Reported lesion symptoms include bothersome appearance and itching, the patient reports the lesion is raised or bumpy, the patient considered this a rash, present for about one day, the front of the torso is involved, the photograph was taken at an angle:
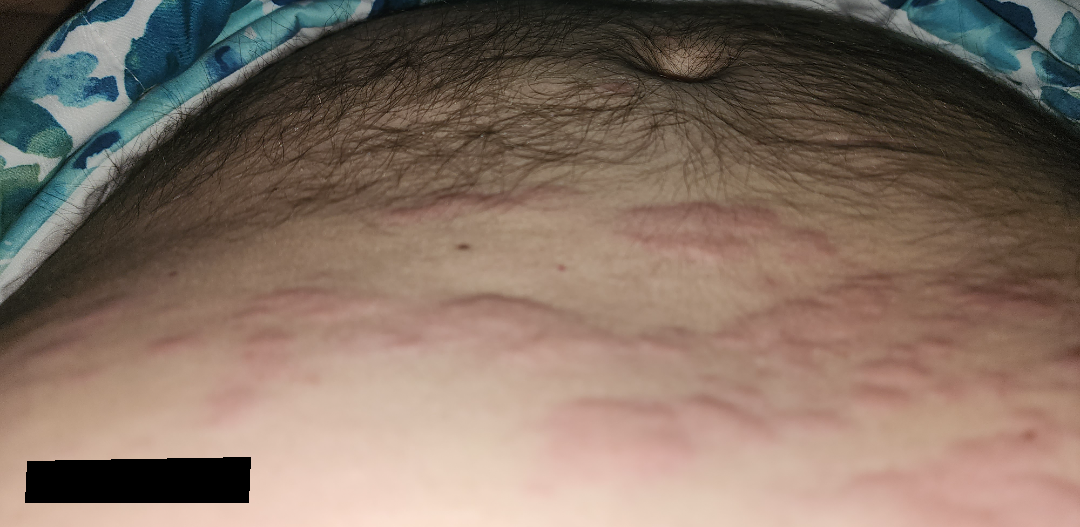differential=most likely Urticaria; an alternative is Allergic Contact Dermatitis.